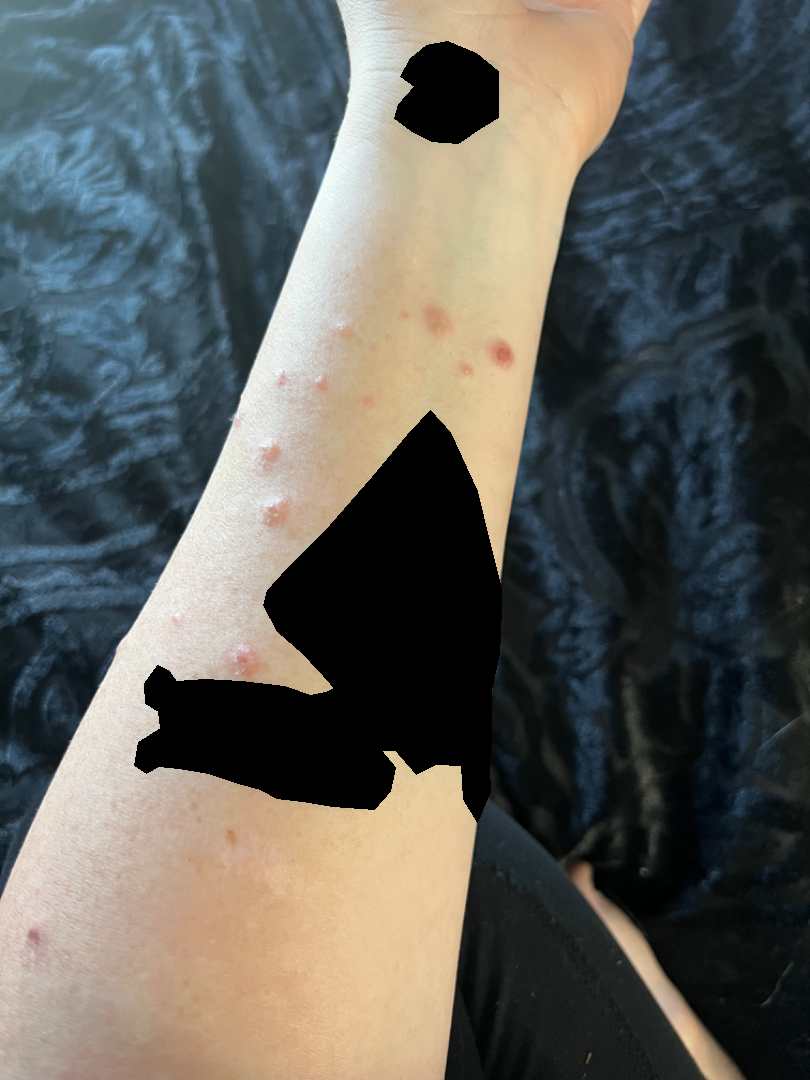Close-up view.
The patient considered this a rash.
The patient indicates the lesion is rough or flaky, fluid-filled and raised or bumpy.
The patient indicates itching, enlargement and bothersome appearance.
The lesion involves the arm, head or neck, back of the torso and front of the torso.
Present for less than one week.
Female contributor, age 18–29.
Single-reviewer assessment: the differential includes Prurigo nodularis, Lymphomatoid papulosis and Pityriasis lichenoides, with no clear leading consideration.